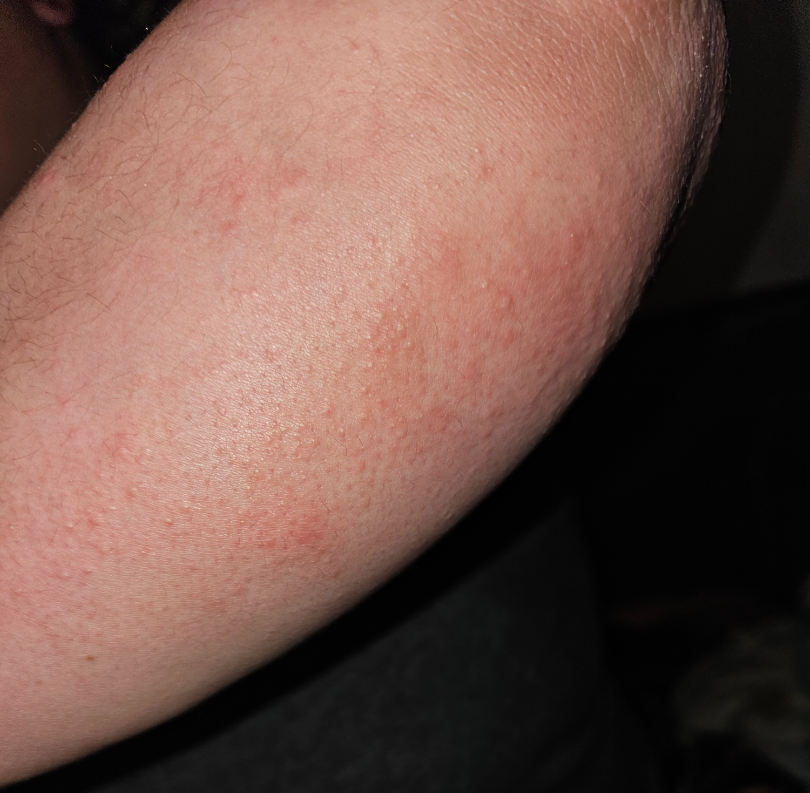The patient considered this a rash.
The photograph is a close-up of the affected area.
Present for about one day.
The arm is involved.
The patient indicates burning, enlargement, pain and itching.
The contributor is a female aged 18–29.
Skin tone: Fitzpatrick II; non-clinician graders estimated Monk skin tone scale 2 or 3 (two reviewer pools).
Eczema and Irritant Contact Dermatitis were considered with similar weight.